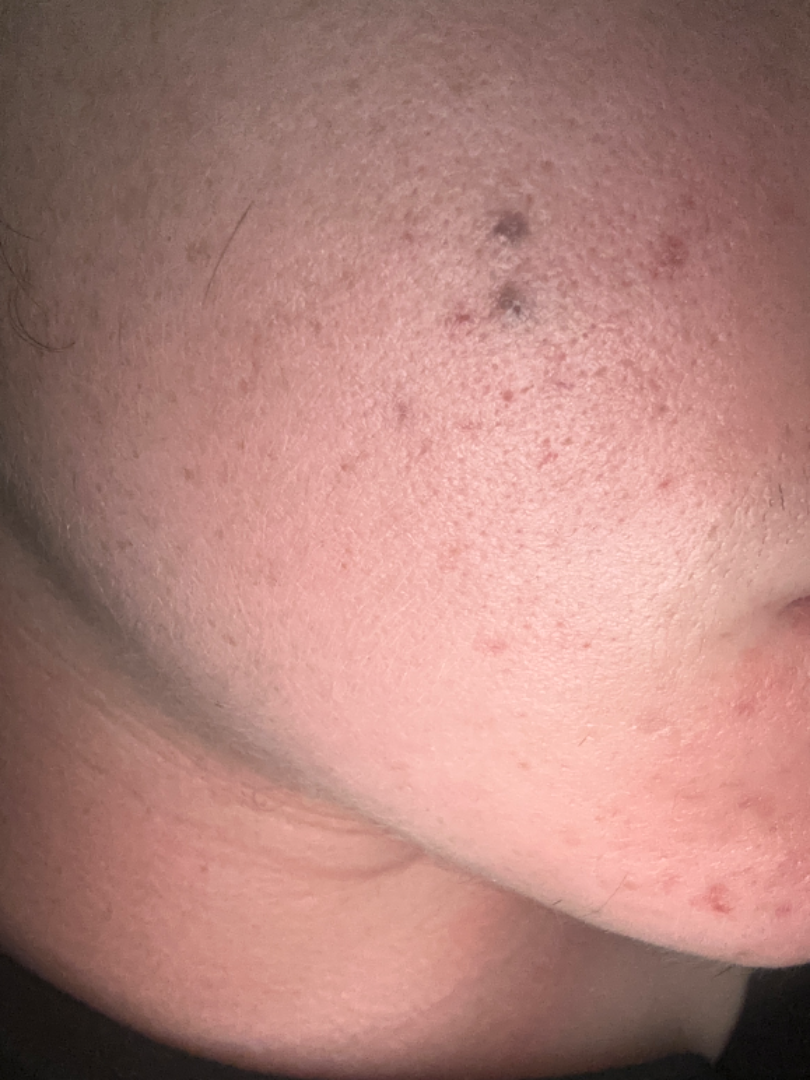{
  "shot_type": "close-up",
  "differential": {
    "leading": [
      "Acne"
    ]
  }
}